A close-up photograph. The subject is a female aged 18–29:
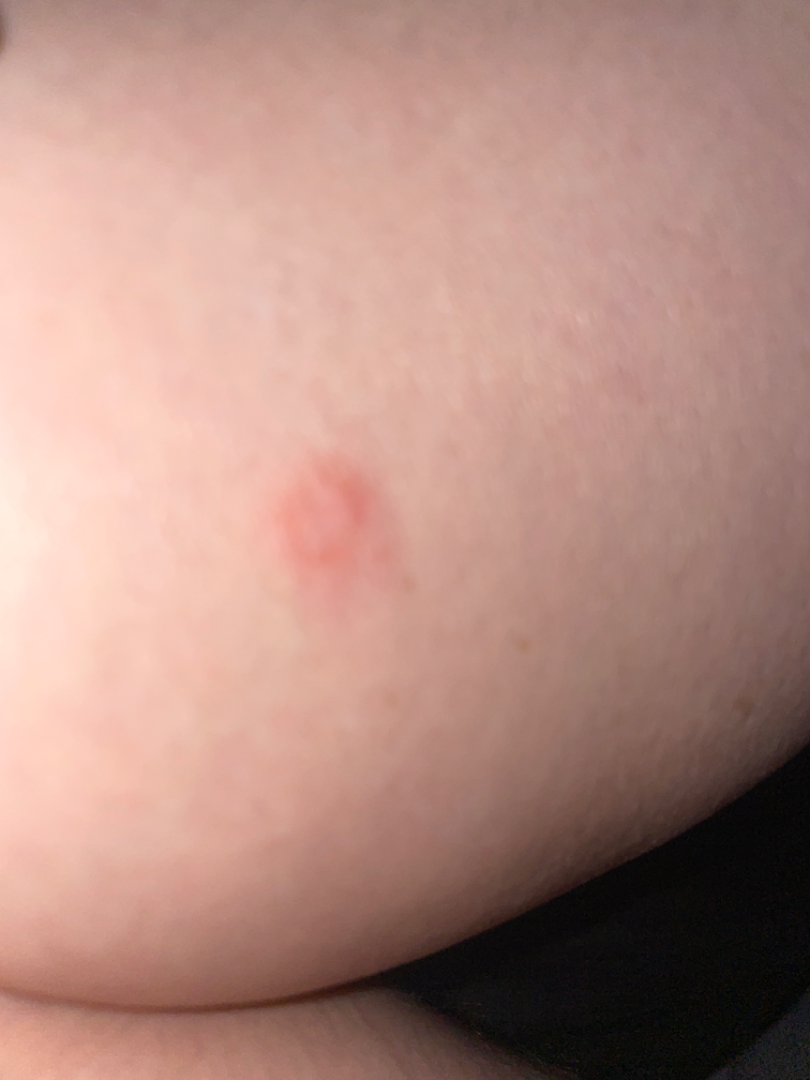assessment=indeterminate